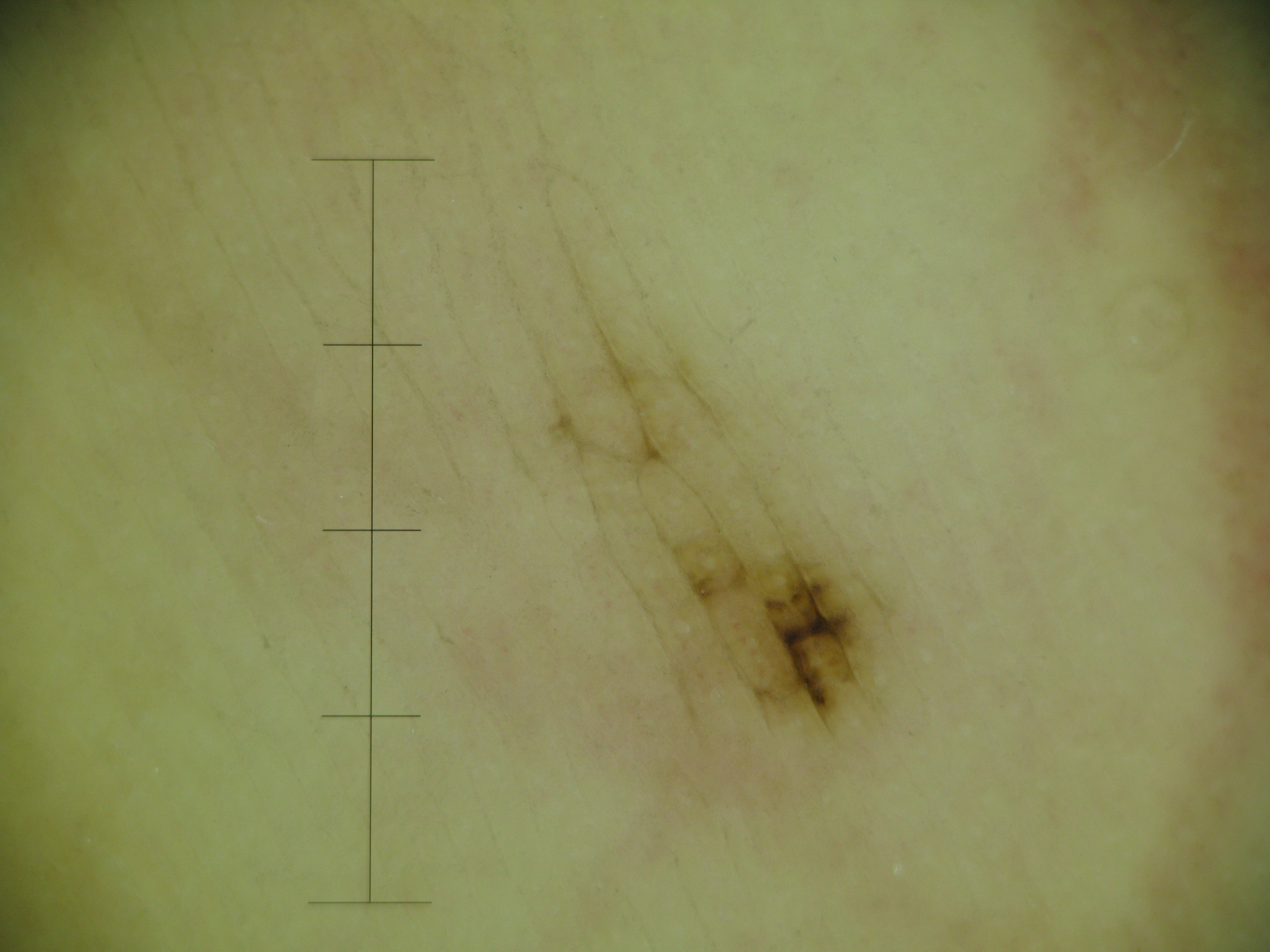Diagnosed as an acral dysplastic junctional nevus.